A dermatoscopic image of a skin lesion: 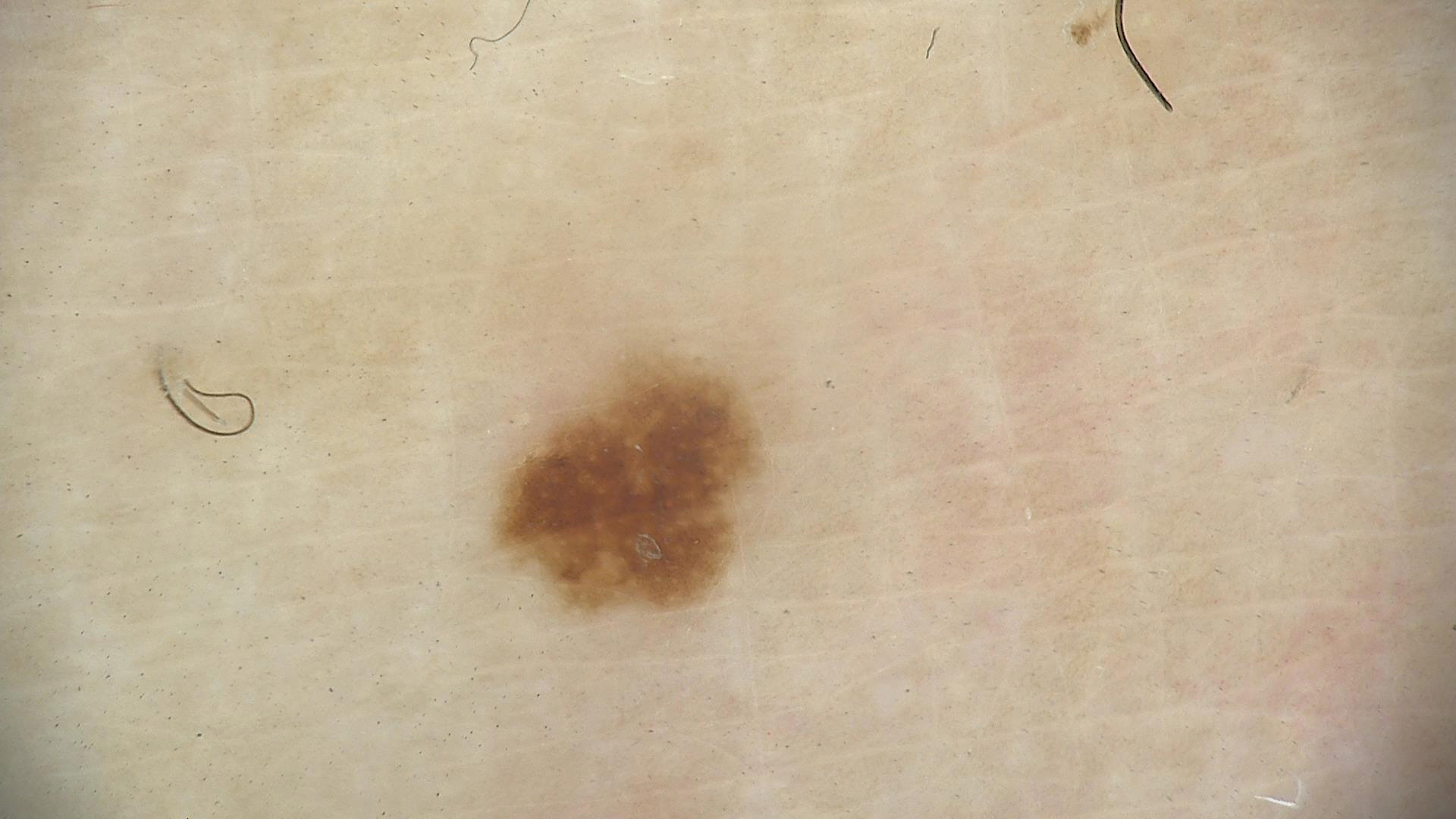Impression:
Labeled as a benign lesion — a dysplastic junctional nevus.